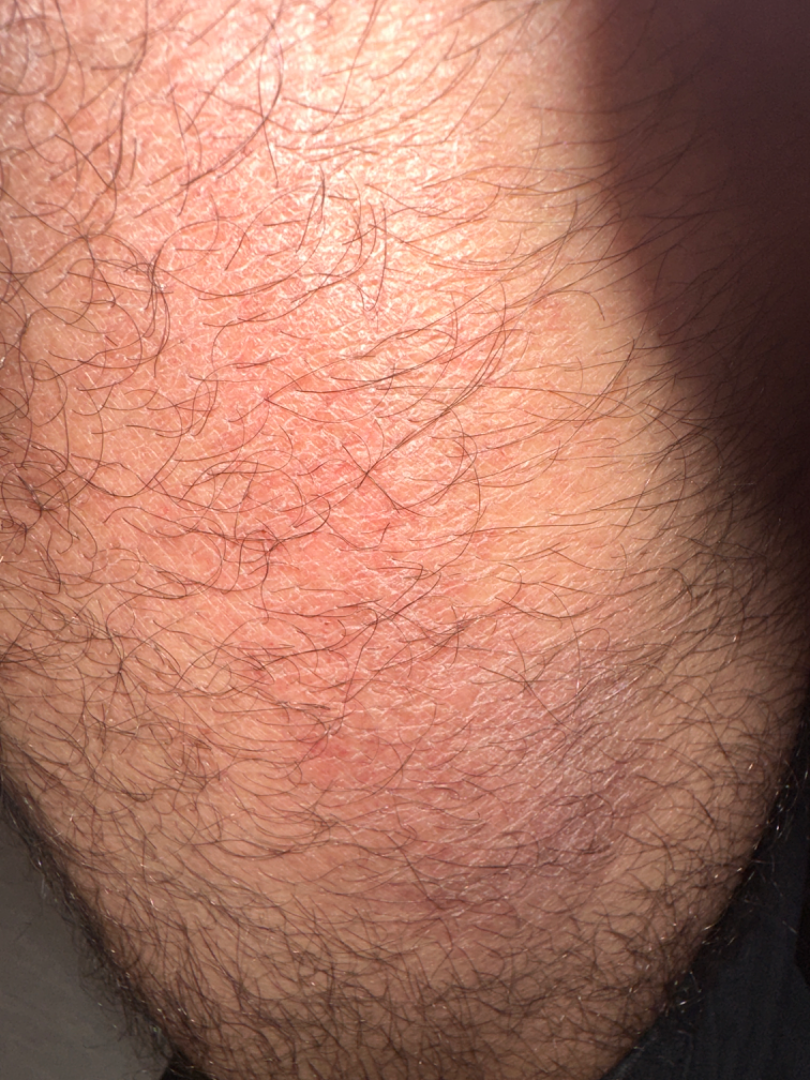Findings:
- diagnostic considerations — most consistent with Acute and chronic dermatitis